Located on the front of the torso · a close-up photograph: 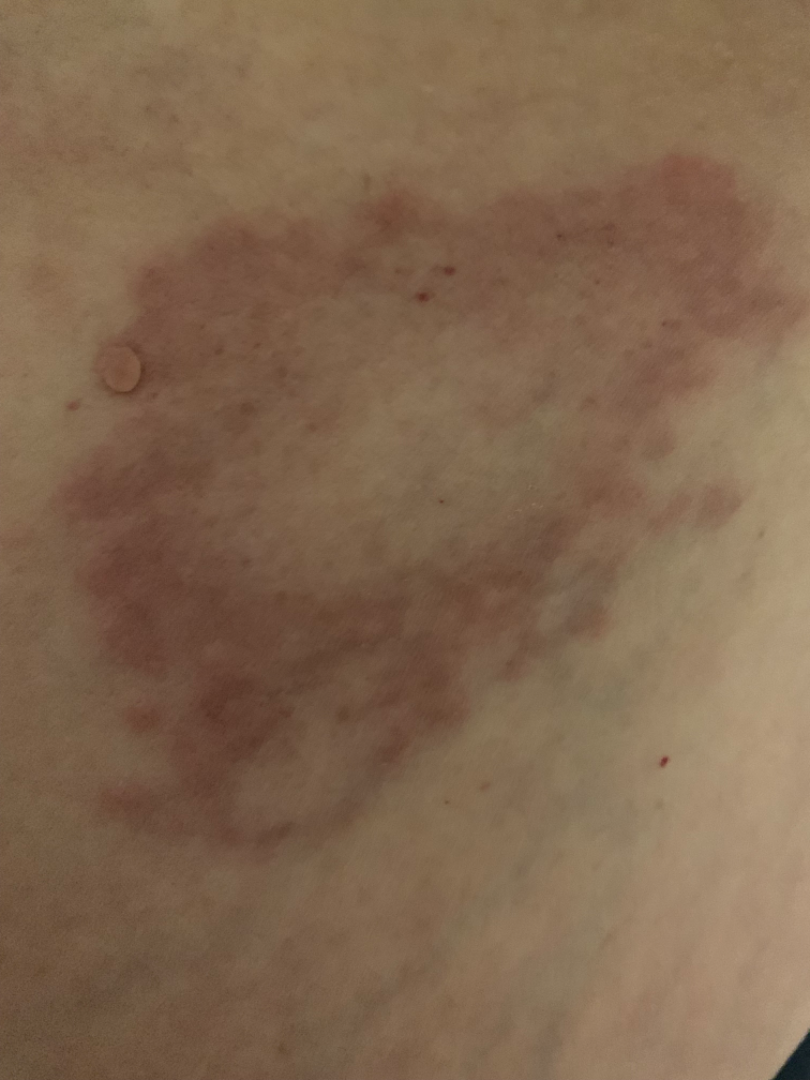| key | value |
|---|---|
| patient-reported symptoms | none reported |
| surface texture | flat |
| duration | three to twelve months |
| constitutional symptoms | none reported |
| impression | in keeping with Granuloma annulare |